The photograph was taken at a distance. FST III; lay graders estimated MST 2. Reported duration is more than one year. The lesion is described as rough or flaky and raised or bumpy.
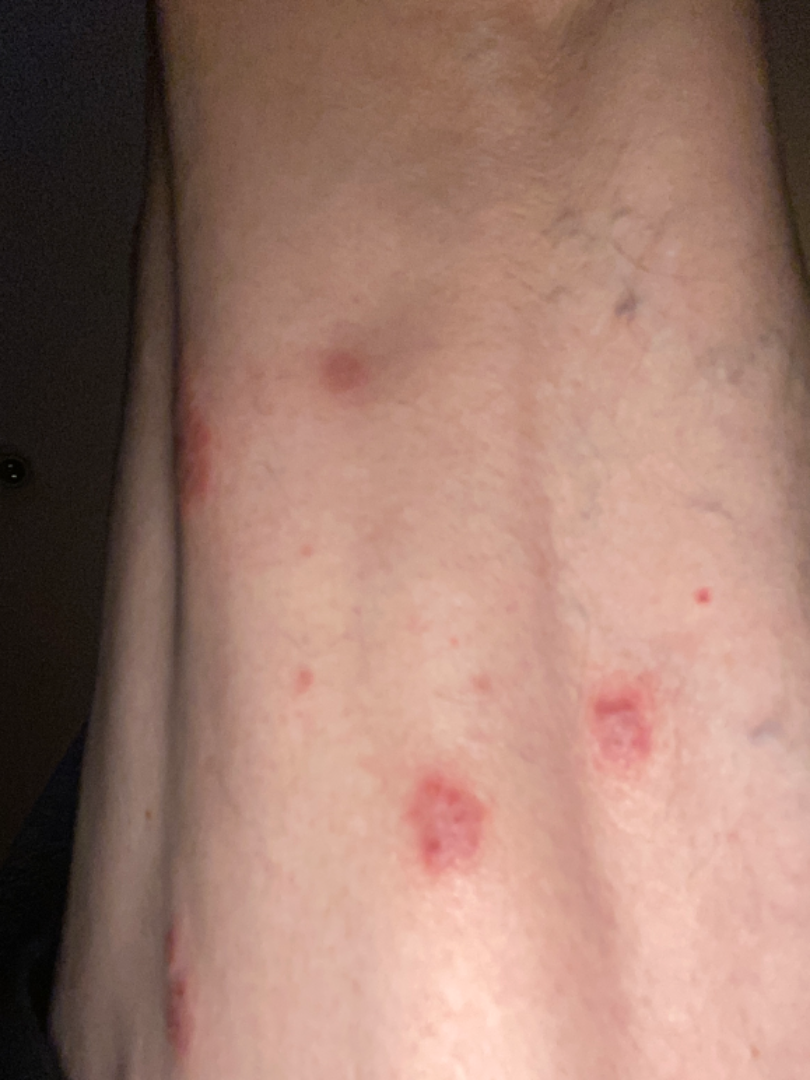The condition could not be reliably identified from the image.